The affected area is the arm; the contributor is a female aged 30–39; the photograph is a close-up of the affected area: 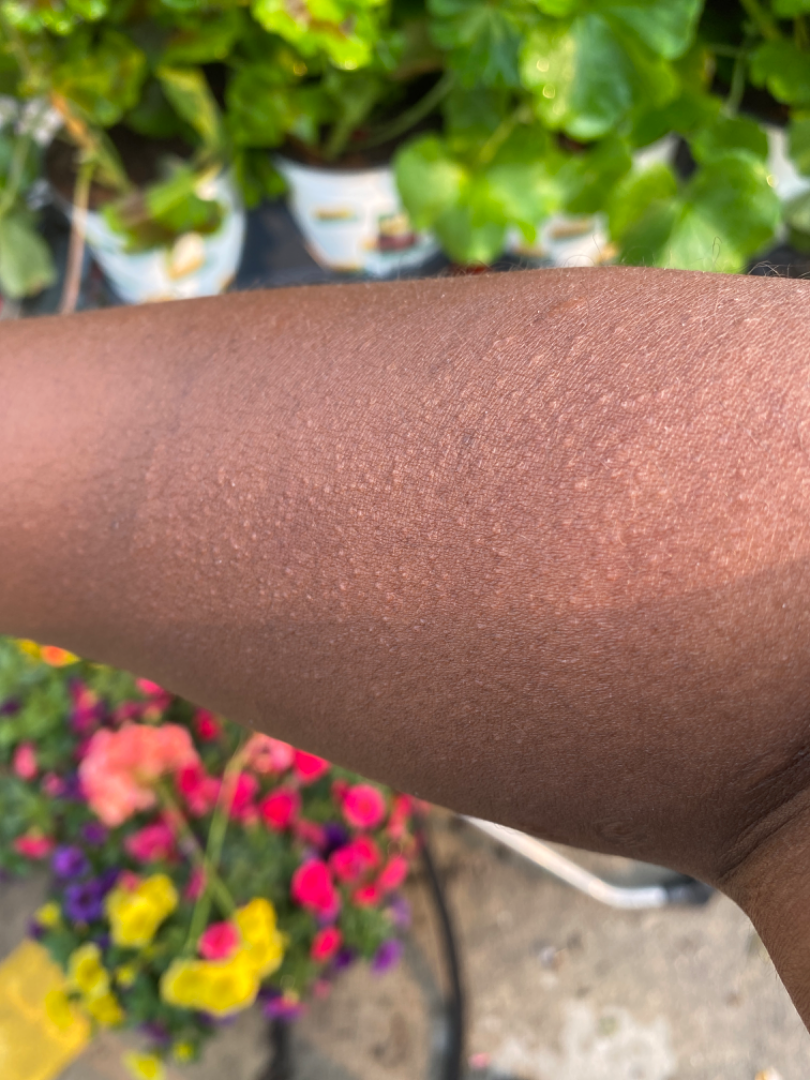Impression: On remote dermatologist review, consistent with Chronic dermatitis, NOS.